The patient indicates the condition has been present for one to three months · the patient indicates the lesion is flat · close-up view · the lesion involves the arm · the patient described the issue as a rash · the subject is a male aged 18–29 · skin tone: Fitzpatrick skin type III; human graders estimated Monk skin tone scale 2–3 · no associated systemic symptoms reported · symptoms reported: bothersome appearance.
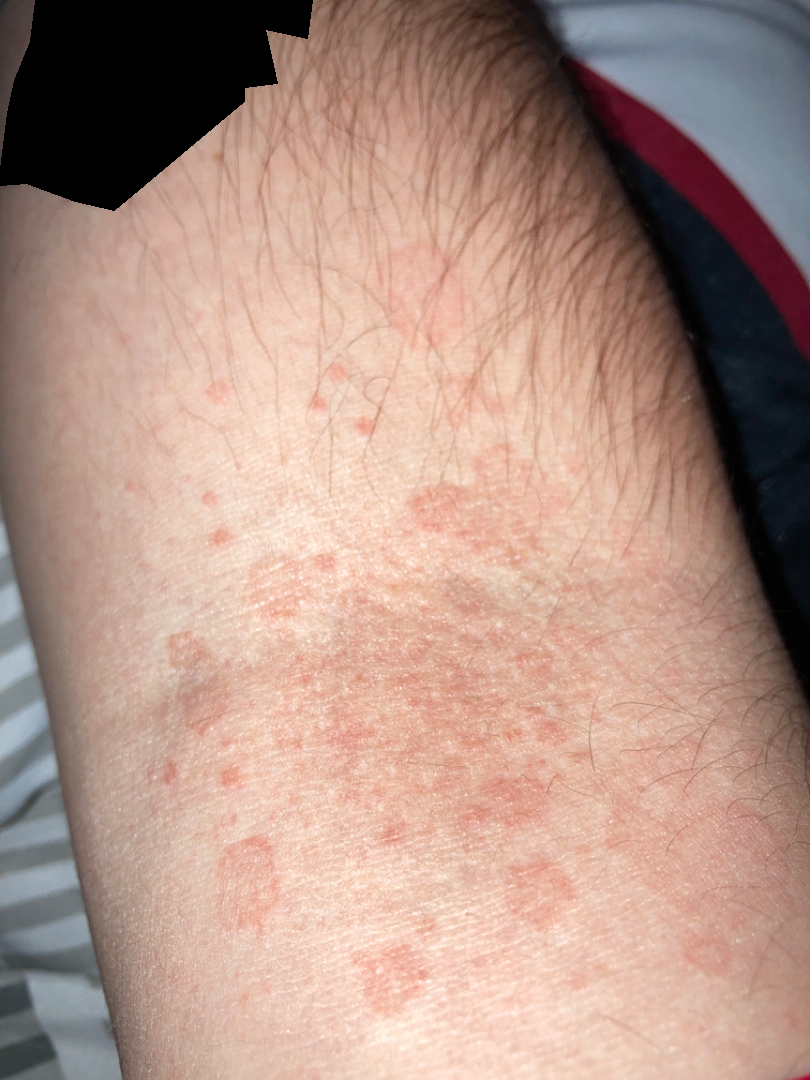Q: What is the dermatologist's impression?
A: the differential, in no particular order, includes Drug Rash, Viral Exanthem and Eczema